The photograph is a close-up of the affected area. The lesion involves the head or neck: 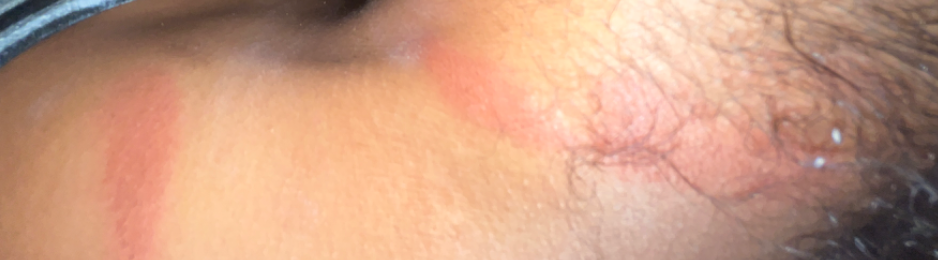{"assessment": "indeterminate", "patient_category": "a rash", "symptoms": ["pain", "burning"], "texture": "raised or bumpy", "skin_tone": {"fitzpatrick": "IV"}, "systemic_symptoms": "none reported", "duration": "about one day"}